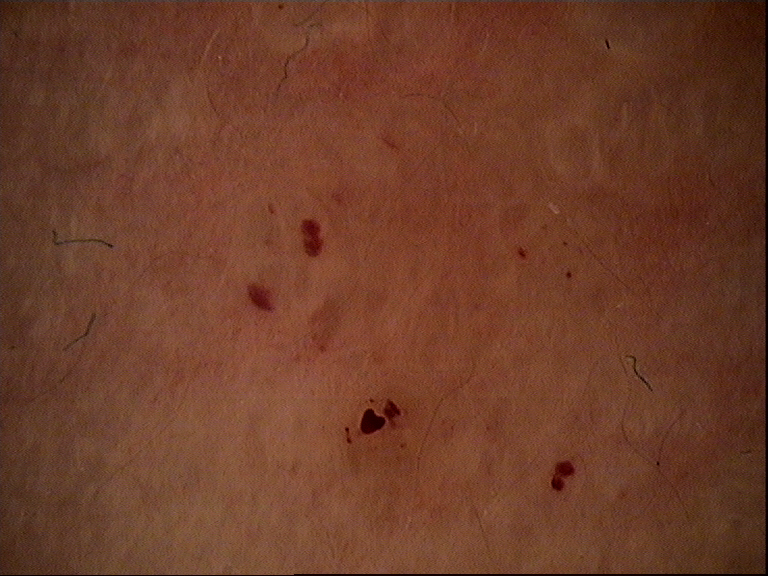This is a vascular lesion. The diagnostic label was a hemangioma.